A dermatoscopic image of a skin lesion.
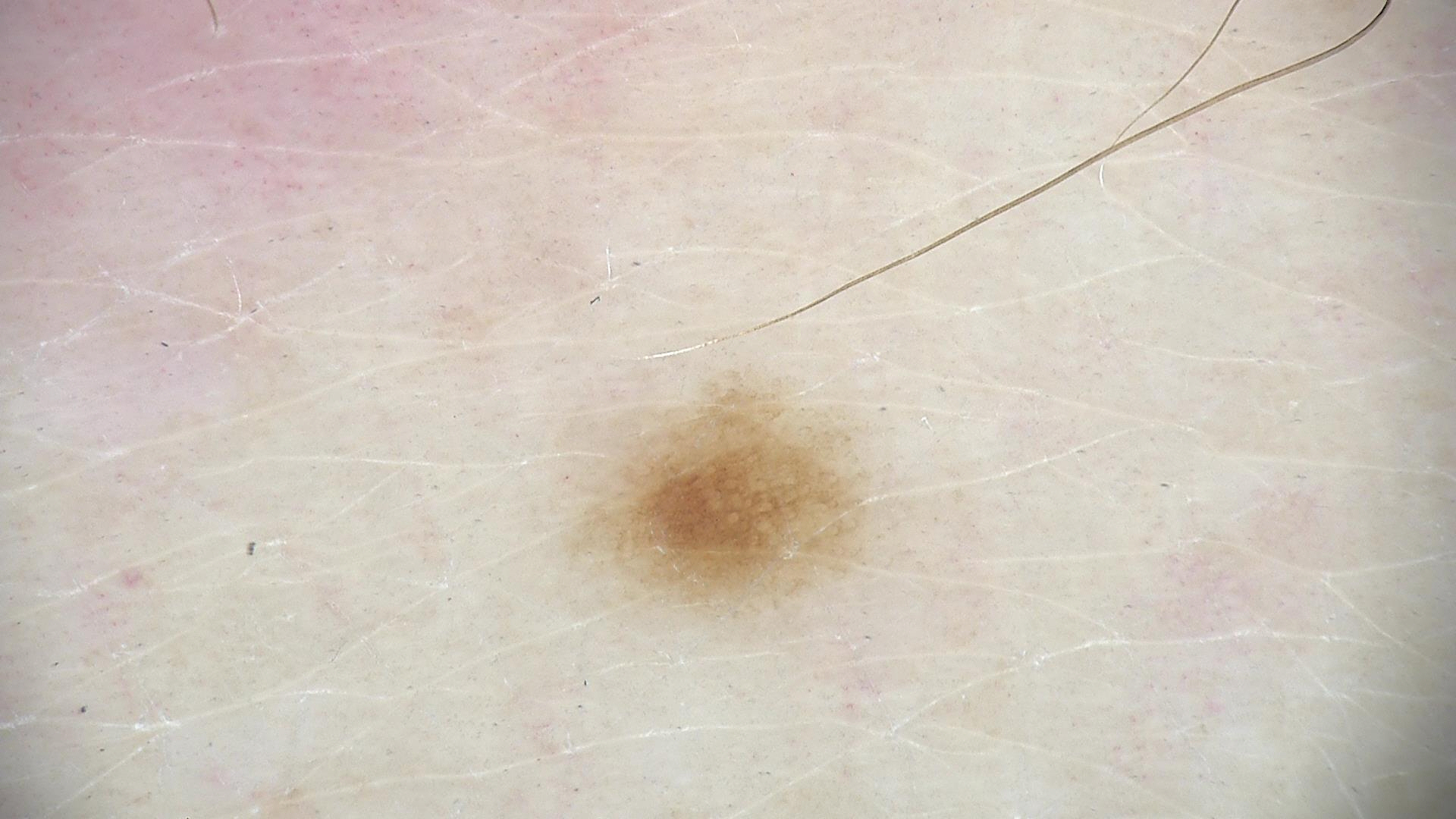Impression:
Diagnosed as a benign lesion — a dysplastic junctional nevus.